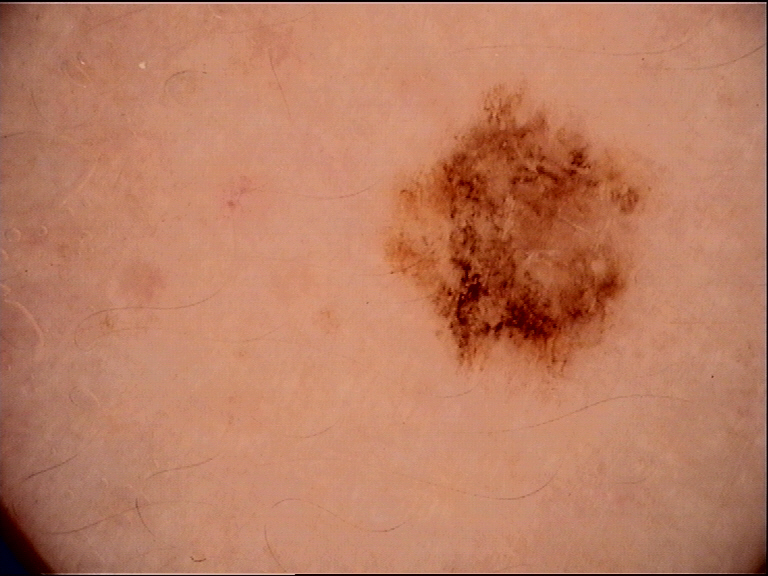Conclusion: Labeled as a dysplastic junctional nevus.